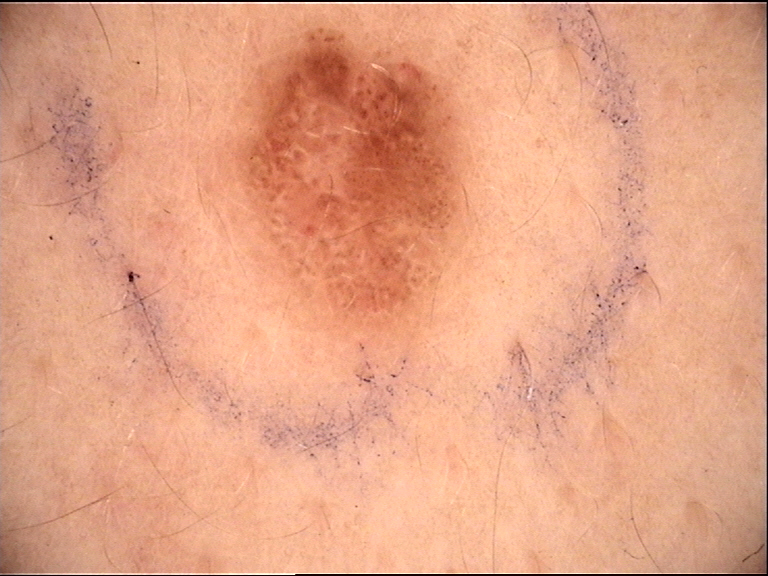Case:
Dermoscopy of a skin lesion.
Impression:
The diagnostic label was a dysplastic compound nevus.